Few moles overall by the patient's own estimate; on a questionnaire the patient reported a personal history of cancer; a male patient 72 years old; a dermoscopic image of a skin lesion; imaged for a research study, with no referral diagnosis recorded; the patient says their skin reddens with sun exposure.
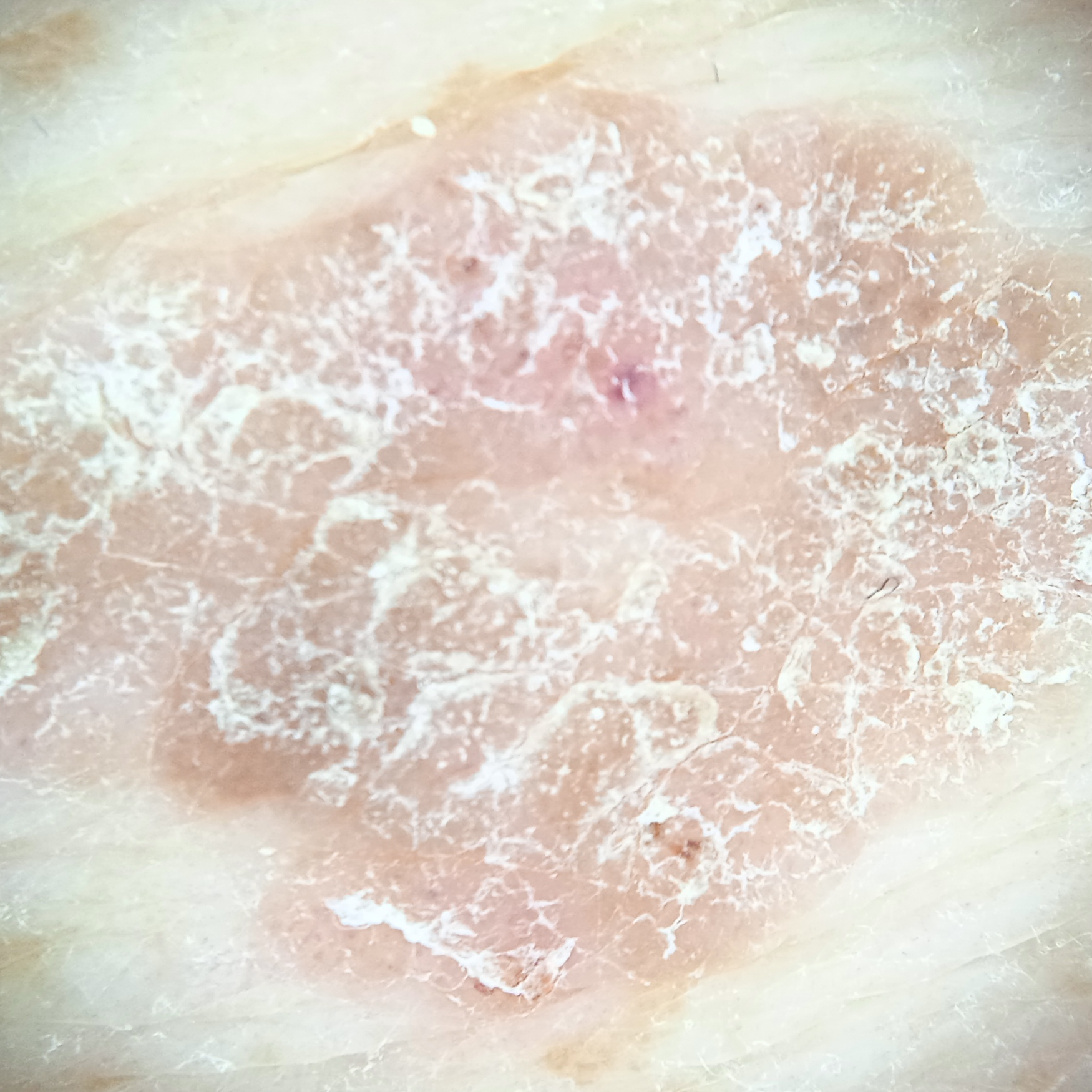Located on the back. The lesion measures approximately 16.5 mm. The consensus diagnosis for this lesion was a seborrheic keratosis.